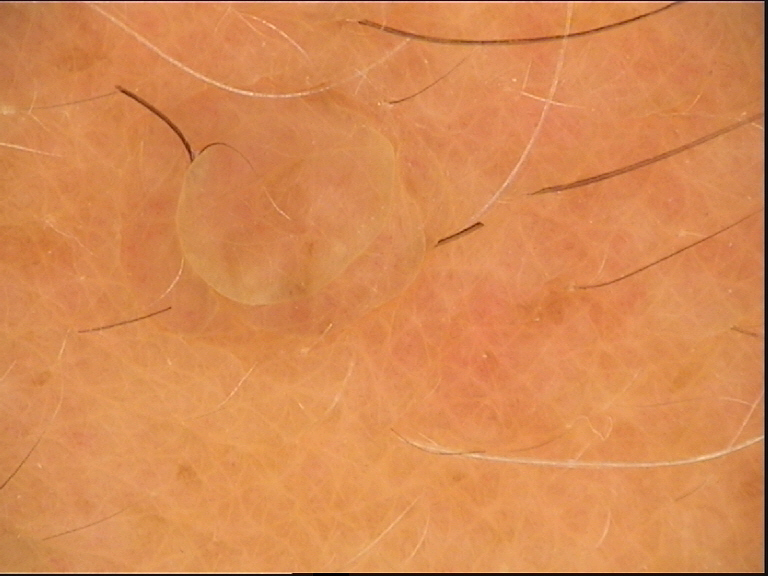image: dermoscopy | assessment: dermal nevus (expert consensus).